A skin lesion imaged with a dermatoscope: 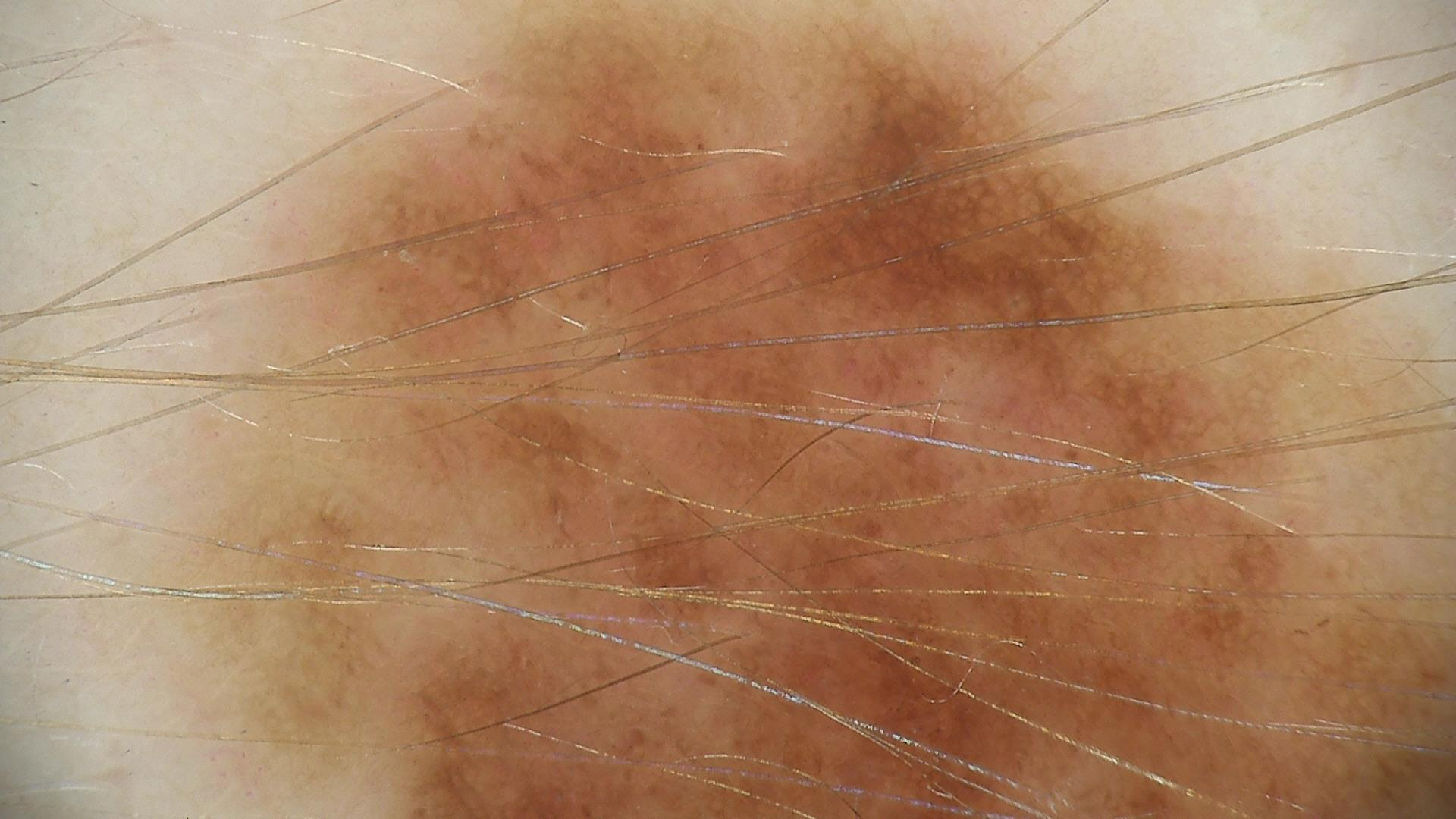{"diagnosis": {"name": "dysplastic junctional nevus", "code": "jd", "malignancy": "benign", "super_class": "melanocytic", "confirmation": "expert consensus"}}